A dermoscopic image of a skin lesion:
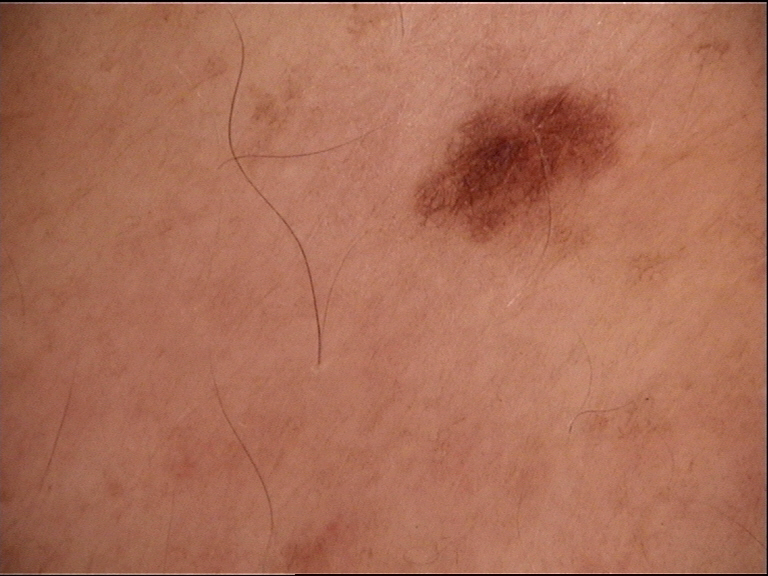Diagnosed as a dysplastic junctional nevus.